A dermatoscopic image of a skin lesion, the patient is a female about 40 years old:
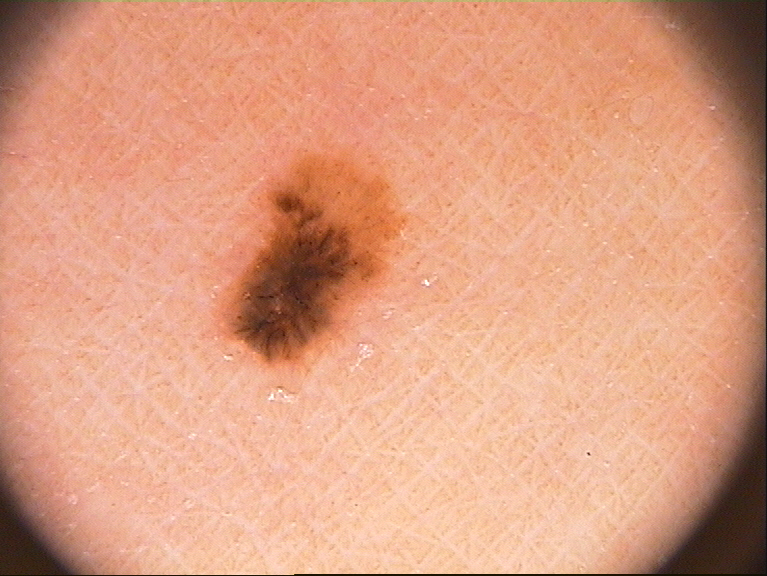Findings:
• dermoscopic findings — streaks and pigment network; absent: milia-like cysts, negative network, and globules
• lesion bbox — 215, 133, 410, 366
• assessment — a melanocytic nevus